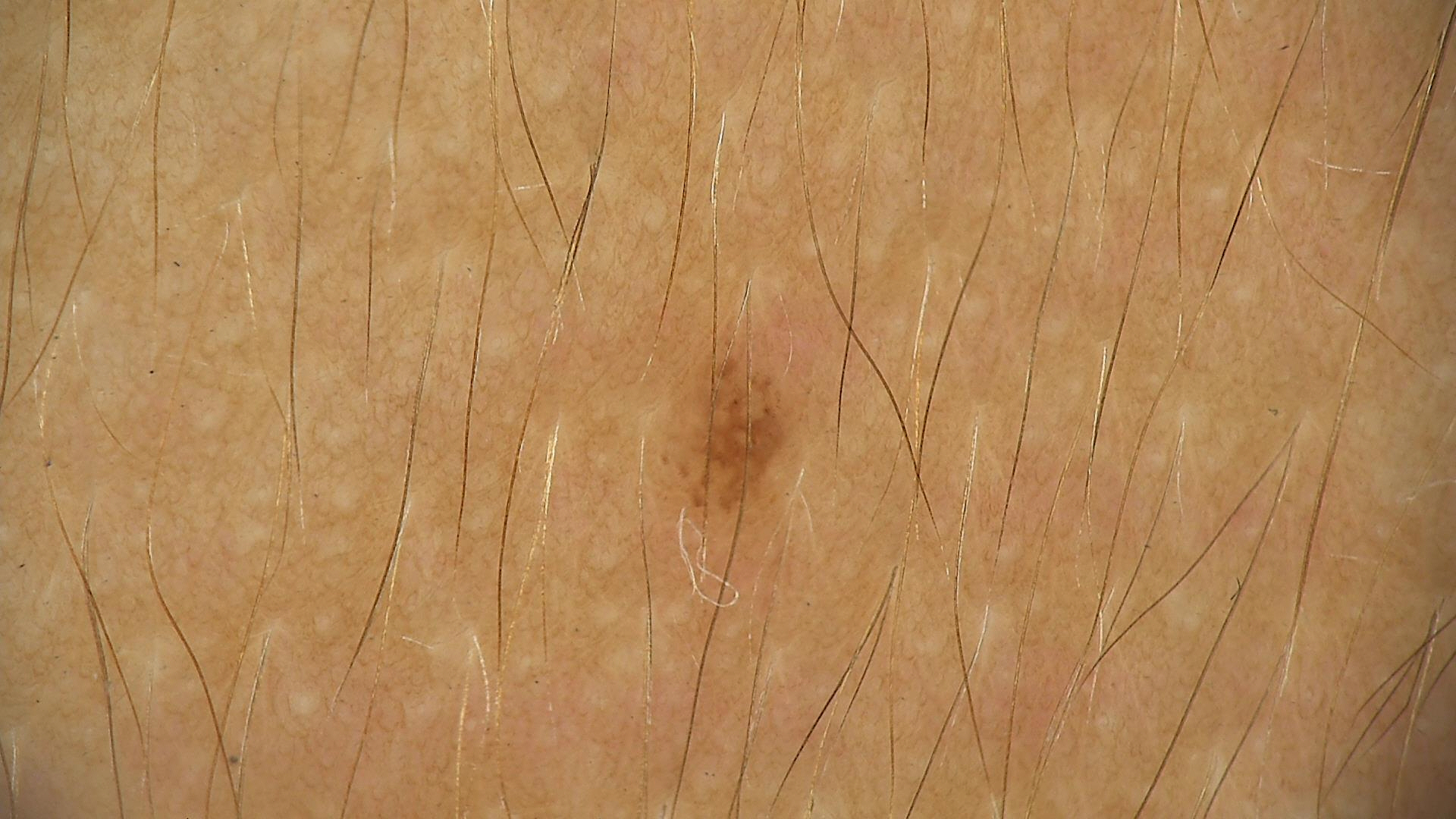Dermoscopy of a skin lesion. Classified as a benign lesion — a dysplastic junctional nevus.